Female subject, age 50–59 · the photo was captured at an angle · the lesion involves the front of the torso and back of the torso: 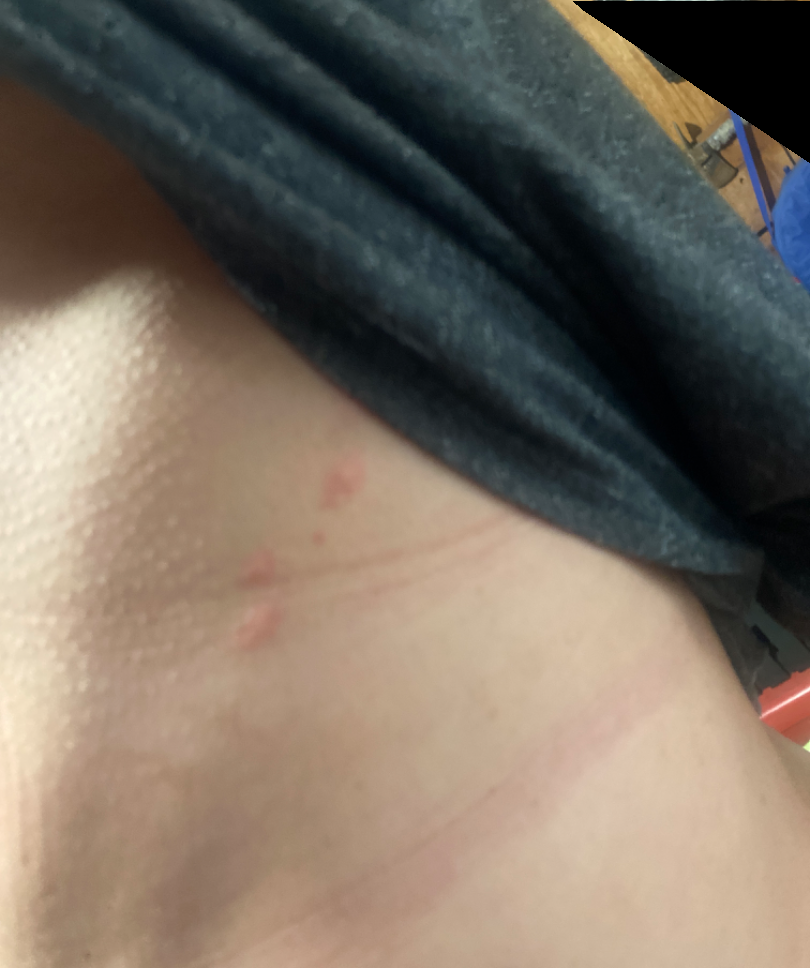Impression:
The dermatologist could not determine a likely condition from the photograph alone.